A patient aged 63. A clinical photograph of a skin lesion:
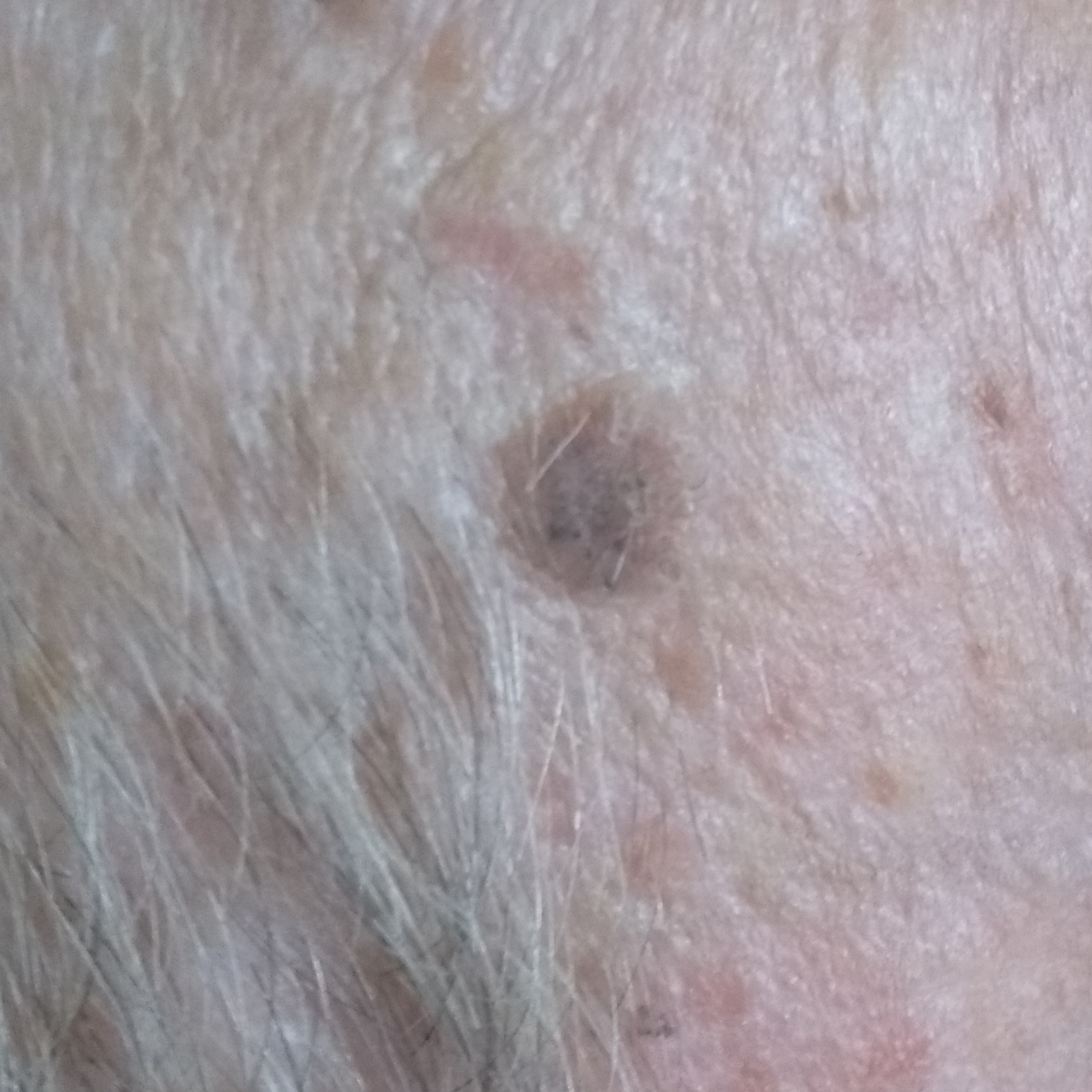location = the face | reported symptoms = growth / no pain, no change in appearance | diagnosis = seborrheic keratosis (clinical consensus).